A male patient, a dermatoscopic image of a skin lesion:
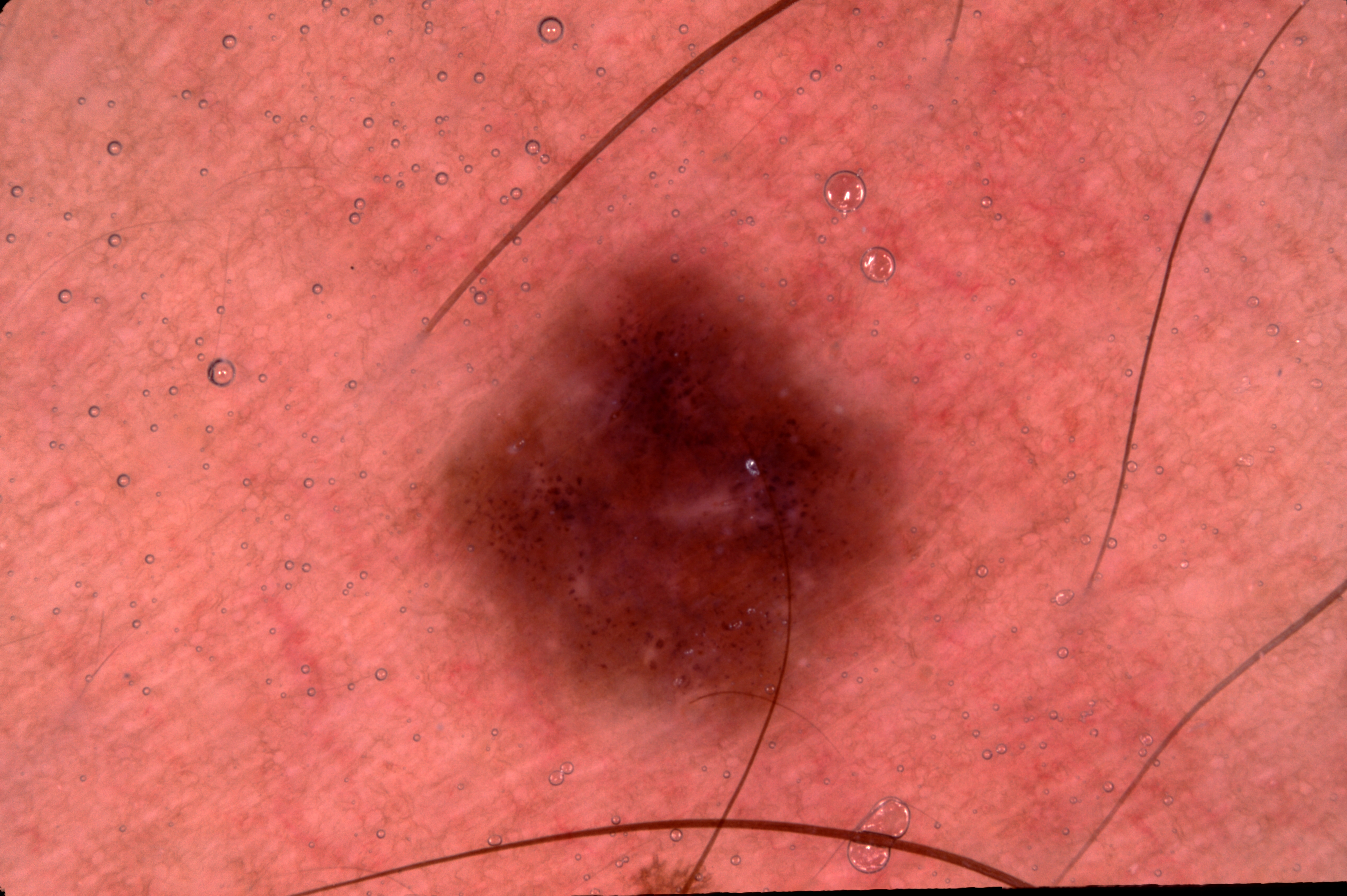Dermoscopic review identifies no milia-like cysts, negative network, pigment network, or streaks.
A moderately sized lesion.
In (x1, y1, x2, y2) order, the lesion is located at <bbox>413, 223, 943, 750</bbox>.
Consistent with a melanocytic nevus, a benign lesion.